The patient was assessed as Fitzpatrick phototype III; the chart notes pesticide exposure; a male patient aged 62; a clinical photograph of a skin lesion: 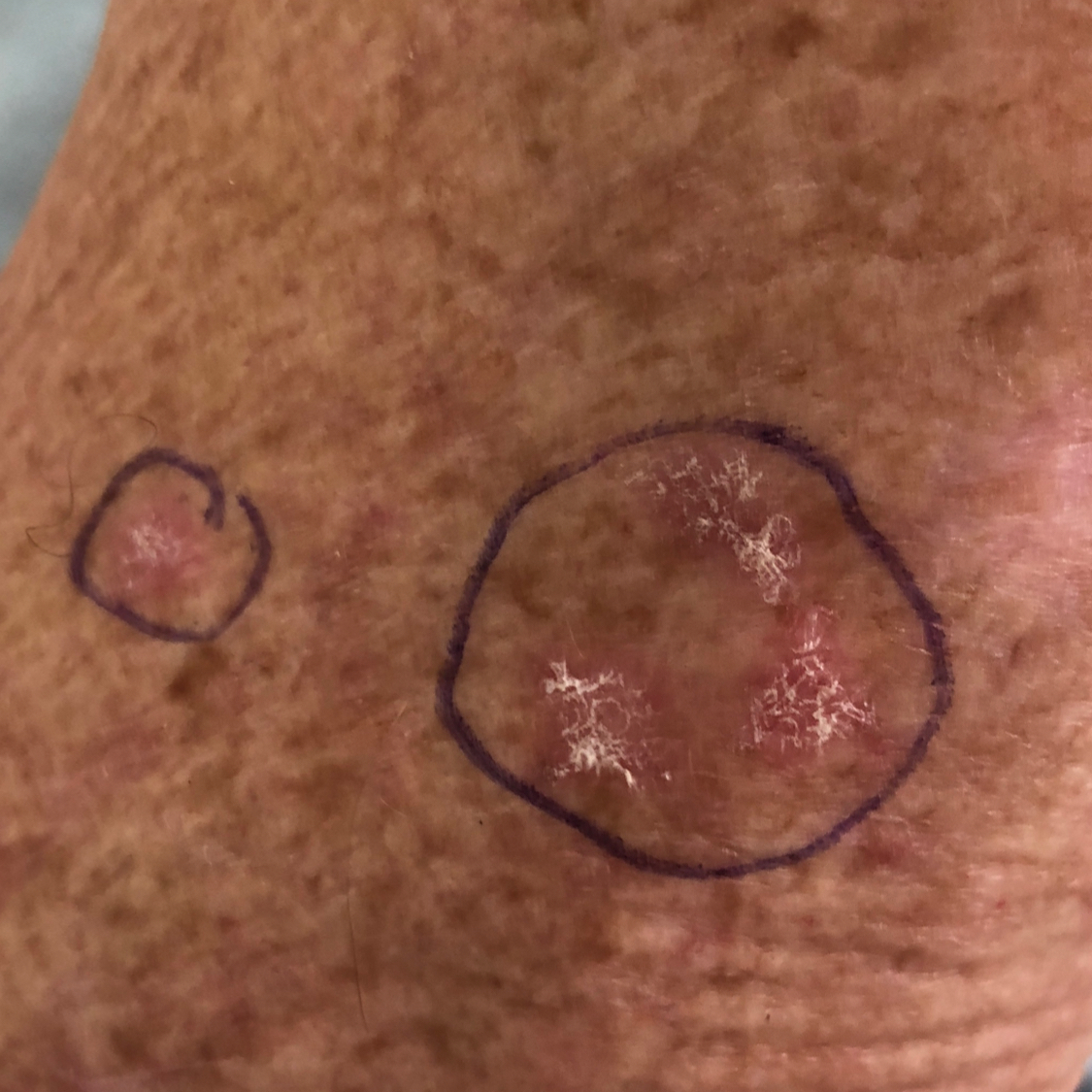Q: Where on the body is the lesion?
A: an arm
Q: What are the lesion's dimensions?
A: 6 × 6 mm
Q: What does the patient describe?
A: itching / no elevation, no pain
Q: What is the diagnosis?
A: actinic keratosis (clinical consensus)